A male patient 72 years old; a clinical close-up of a skin lesion; the patient describes having a moderate number of moles — 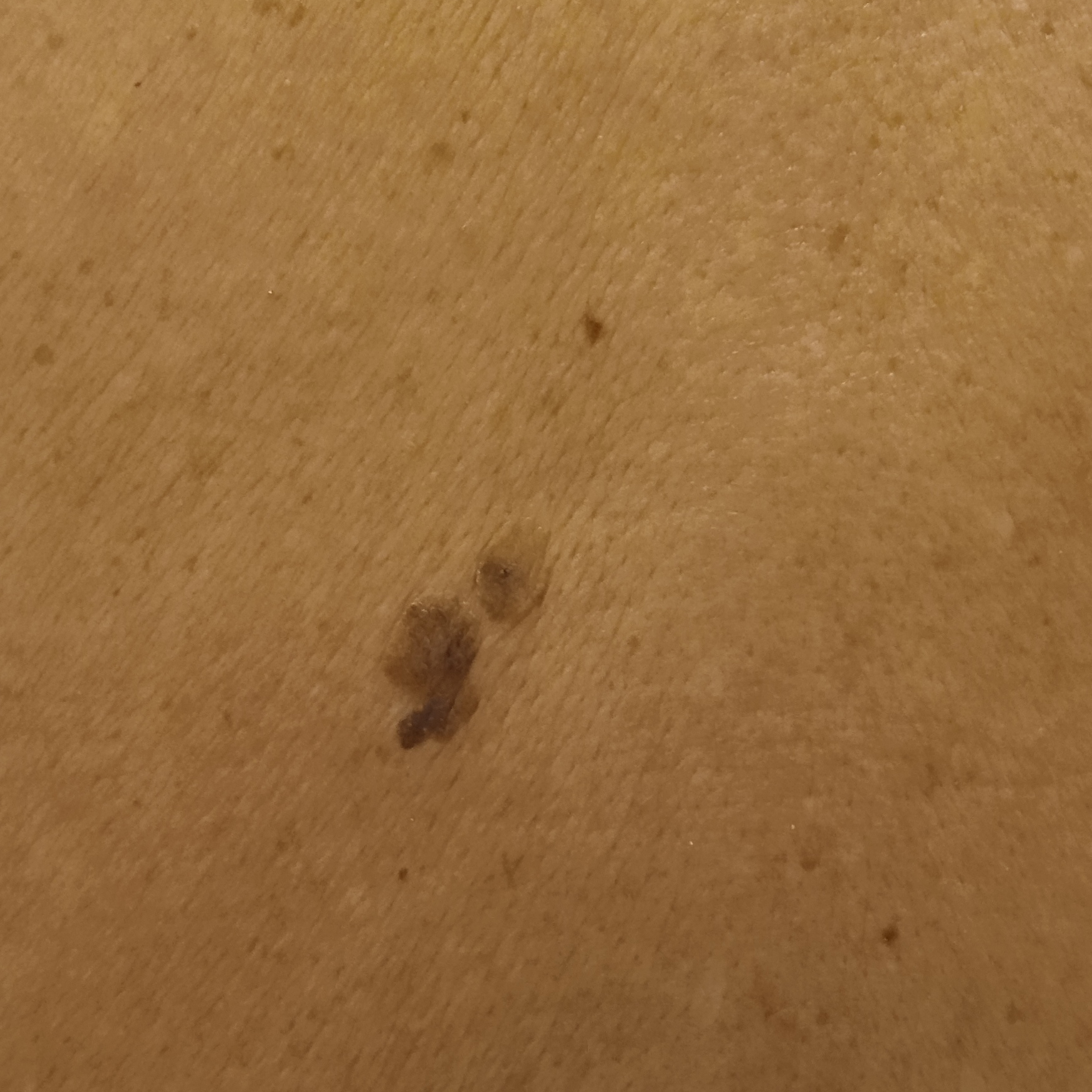diameter: 12.8 mm | diagnostic label: seborrheic keratosis (dermatologist consensus).